A dermoscopy image of a single skin lesion.
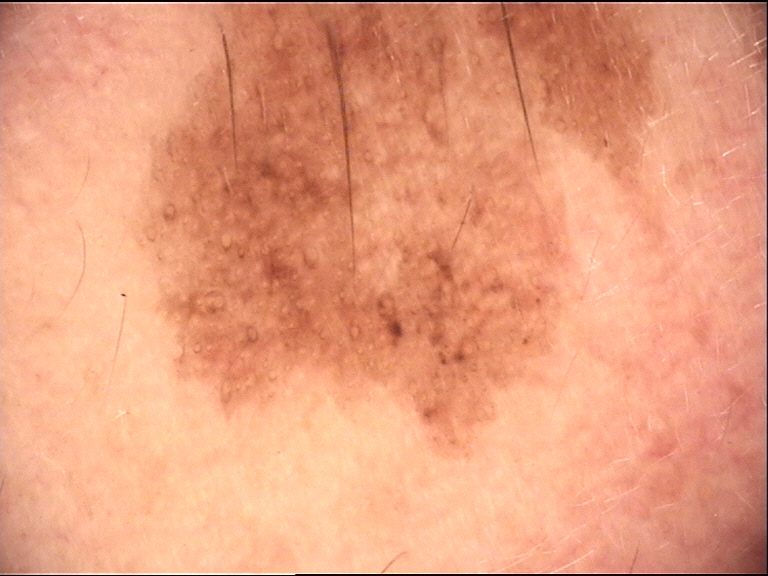Confirmed on histopathology as a skin cancer — a lentigo maligna.